FST II · a female subject aged 73 · a clinical photo of a skin lesion taken with a smartphone · the chart records prior skin cancer (patient or family):
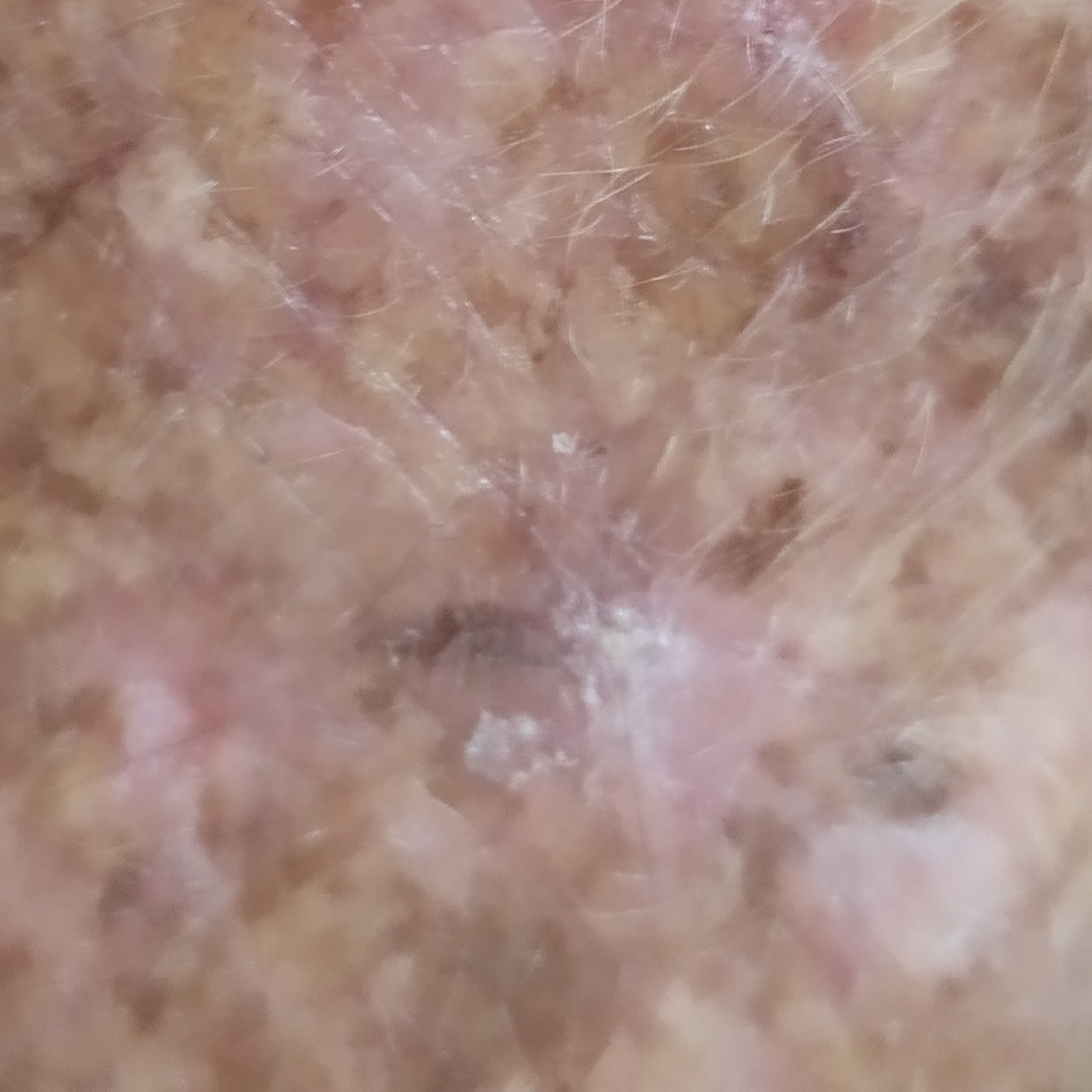{"lesion_location": "a forearm", "lesion_size": {"diameter_1_mm": 12.0, "diameter_2_mm": 6.0}, "symptoms": {"present": ["itching"], "absent": ["change in appearance"]}, "diagnosis": {"name": "actinic keratosis", "code": "ACK", "malignancy": "indeterminate", "confirmation": "clinical consensus"}}